This is a dermoscopic photograph of a skin lesion.
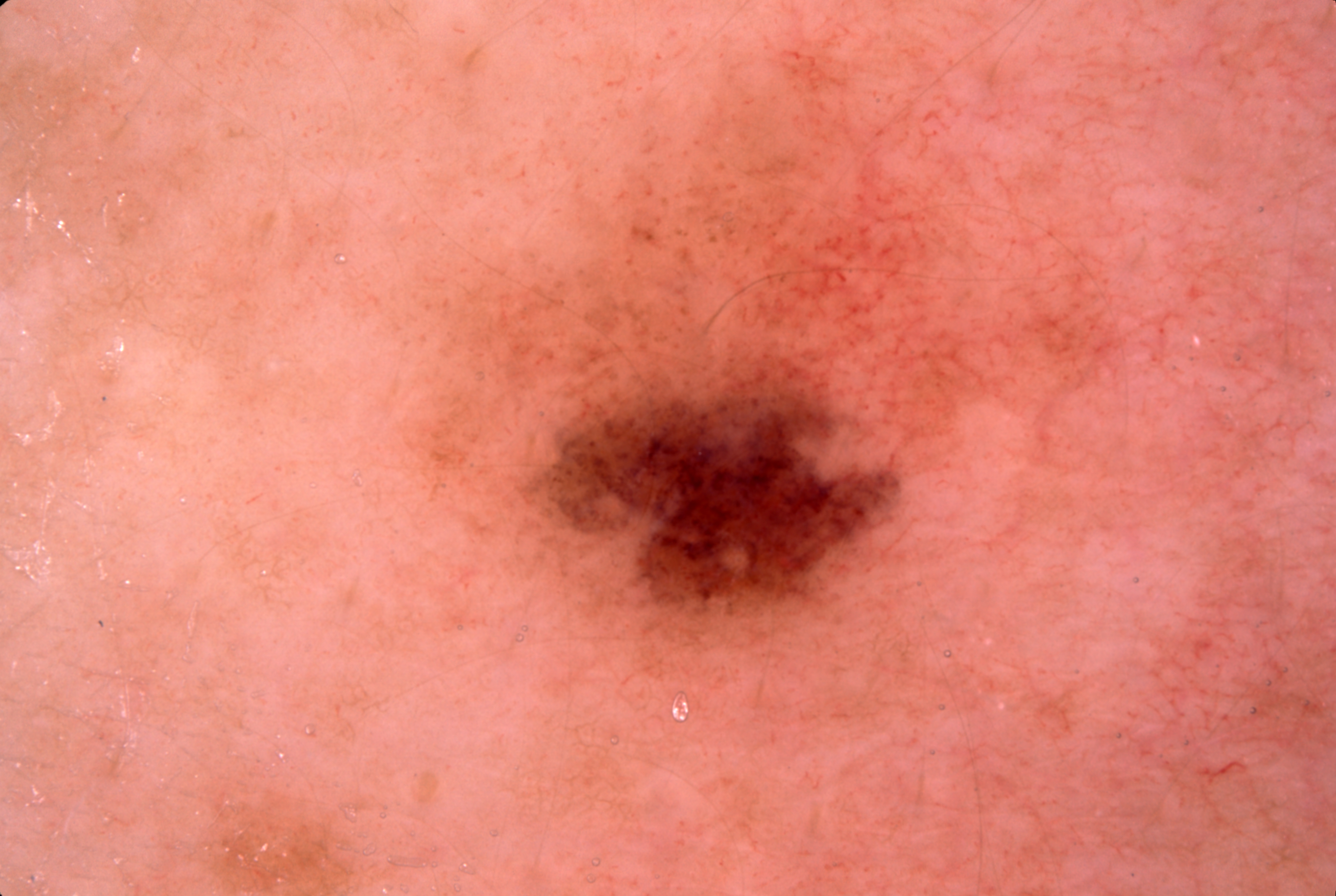- dermoscopic features — milia-like cysts; absent: streaks, negative network, and pigment network
- lesion bbox — [418, 56, 1117, 679]
- lesion extent — ~21% of the field
- assessment — a melanocytic nevus